The chart notes prior malignancy (patient or family), tobacco use, and pesticide exposure:
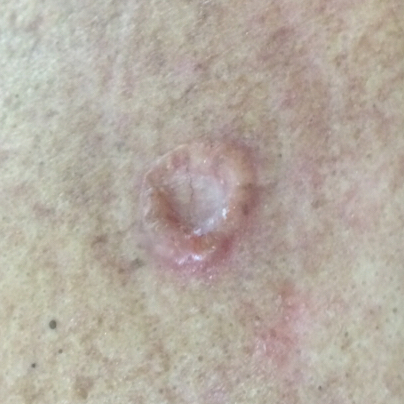The lesion is roughly 19 by 17 mm.
The patient reports that the lesion is elevated, has changed, hurts, has grown, and itches, but has not bled.
Histopathology confirmed a malignancy — a basal cell carcinoma.